A male subject aged around 70 · the patient is skin type III · the chart documents no first-degree relative with melanoma and no previous melanoma · a wide-field clinical photograph of a skin lesion: 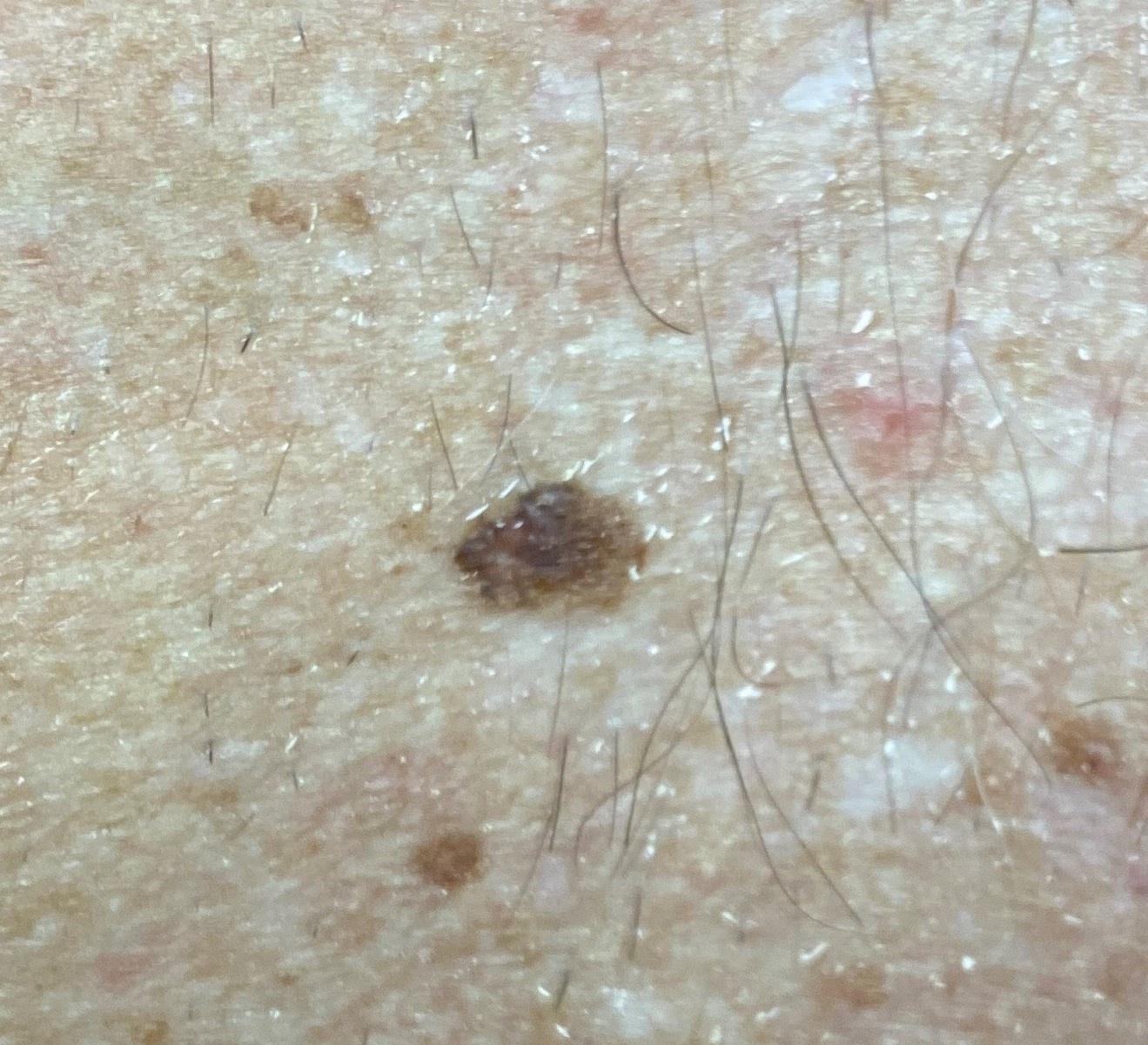Q: Where is the lesion located?
A: the trunk (the anterior trunk)
Q: What did the workup show?
A: Melanoma (biopsy-proven)